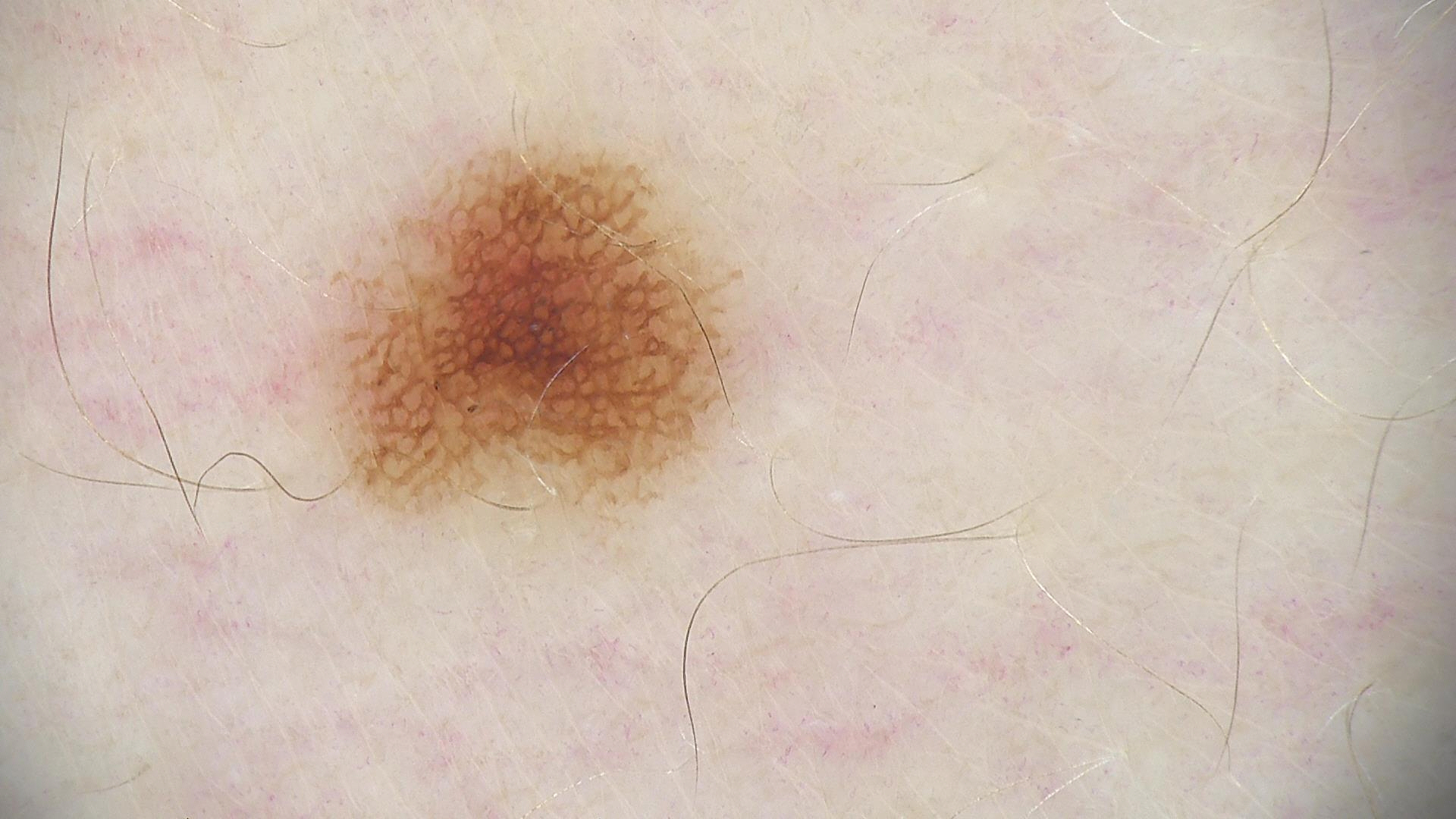A skin lesion imaged with a dermatoscope.
The diagnosis was a dysplastic junctional nevus.